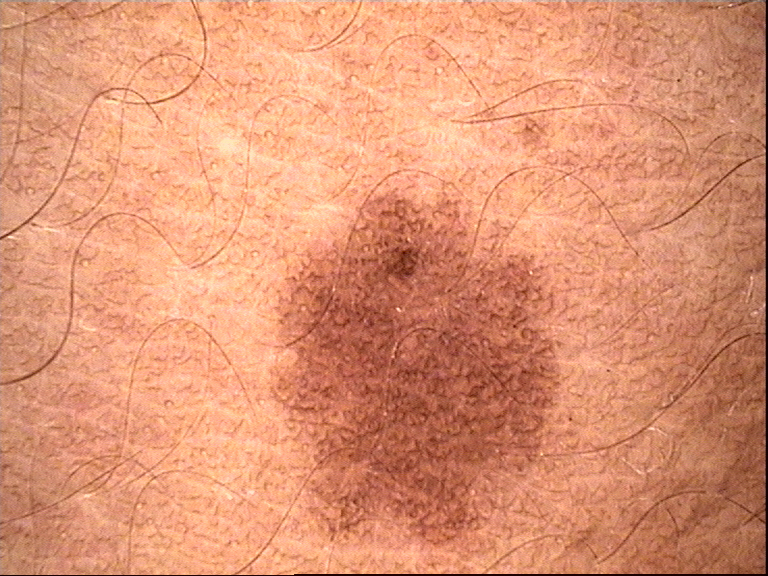Case:
– label: dysplastic junctional nevus (expert consensus)